The photo was captured at an angle: 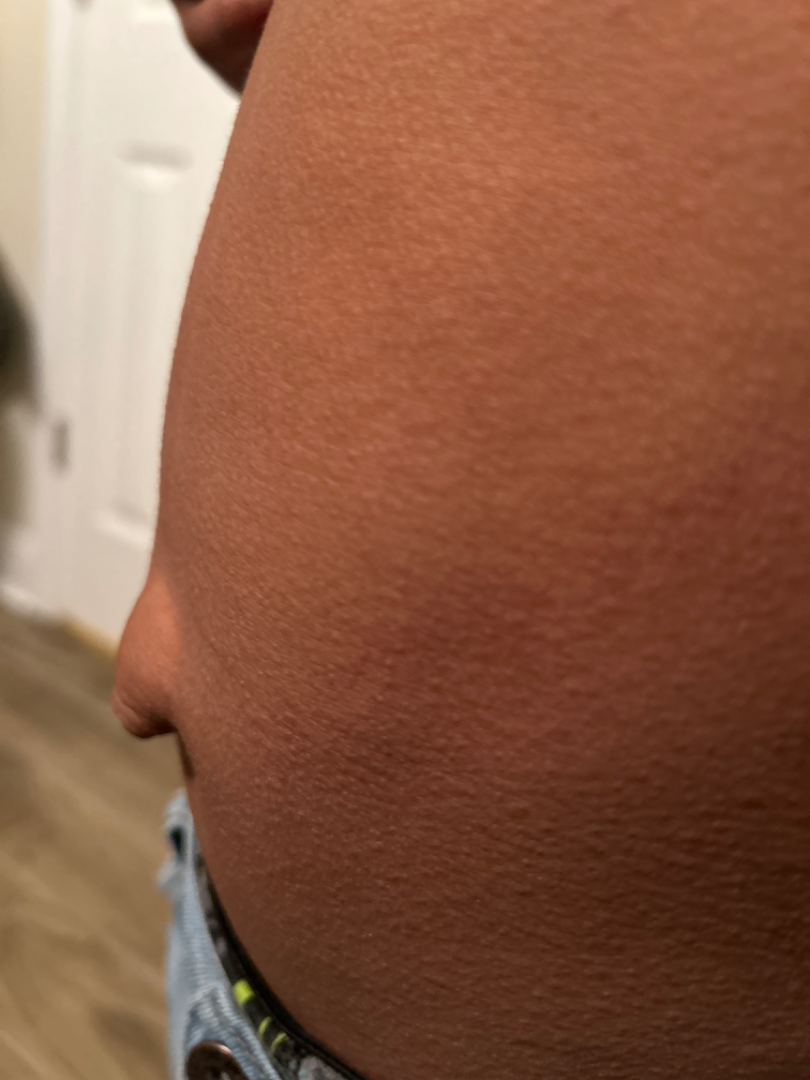Impression: Keratosis pilaris and Eczema were considered with similar weight.